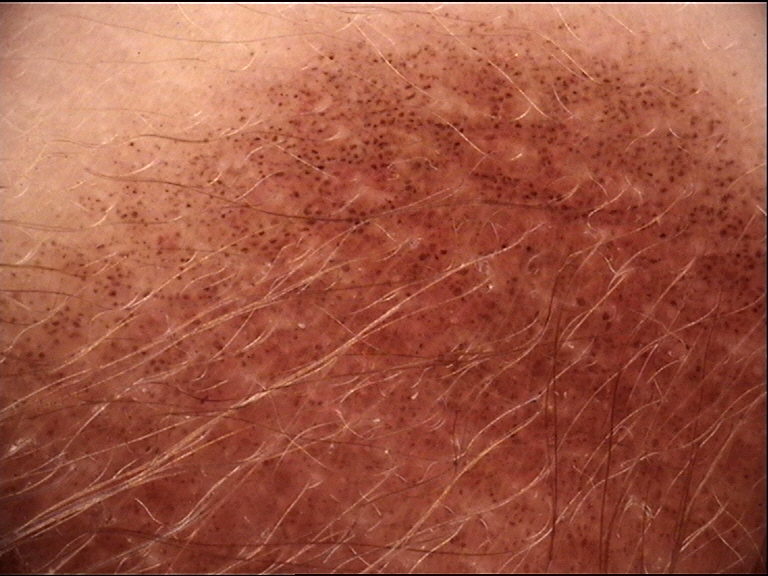  image: dermatoscopy
  diagnosis:
    name: congenital junctional nevus
    code: cjb
    malignancy: benign
    super_class: melanocytic
    confirmation: expert consensus